A dermatoscopic image of a skin lesion:
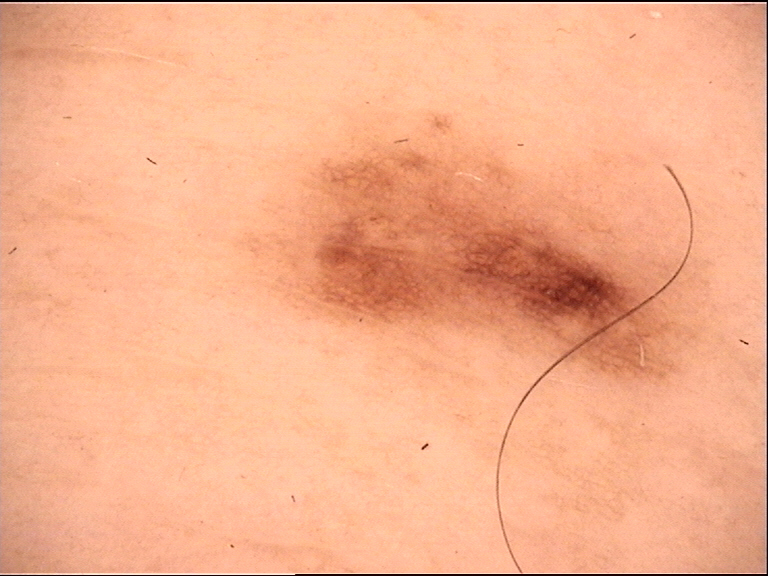Consistent with a dysplastic junctional nevus.